A dermoscopic close-up of a skin lesion.
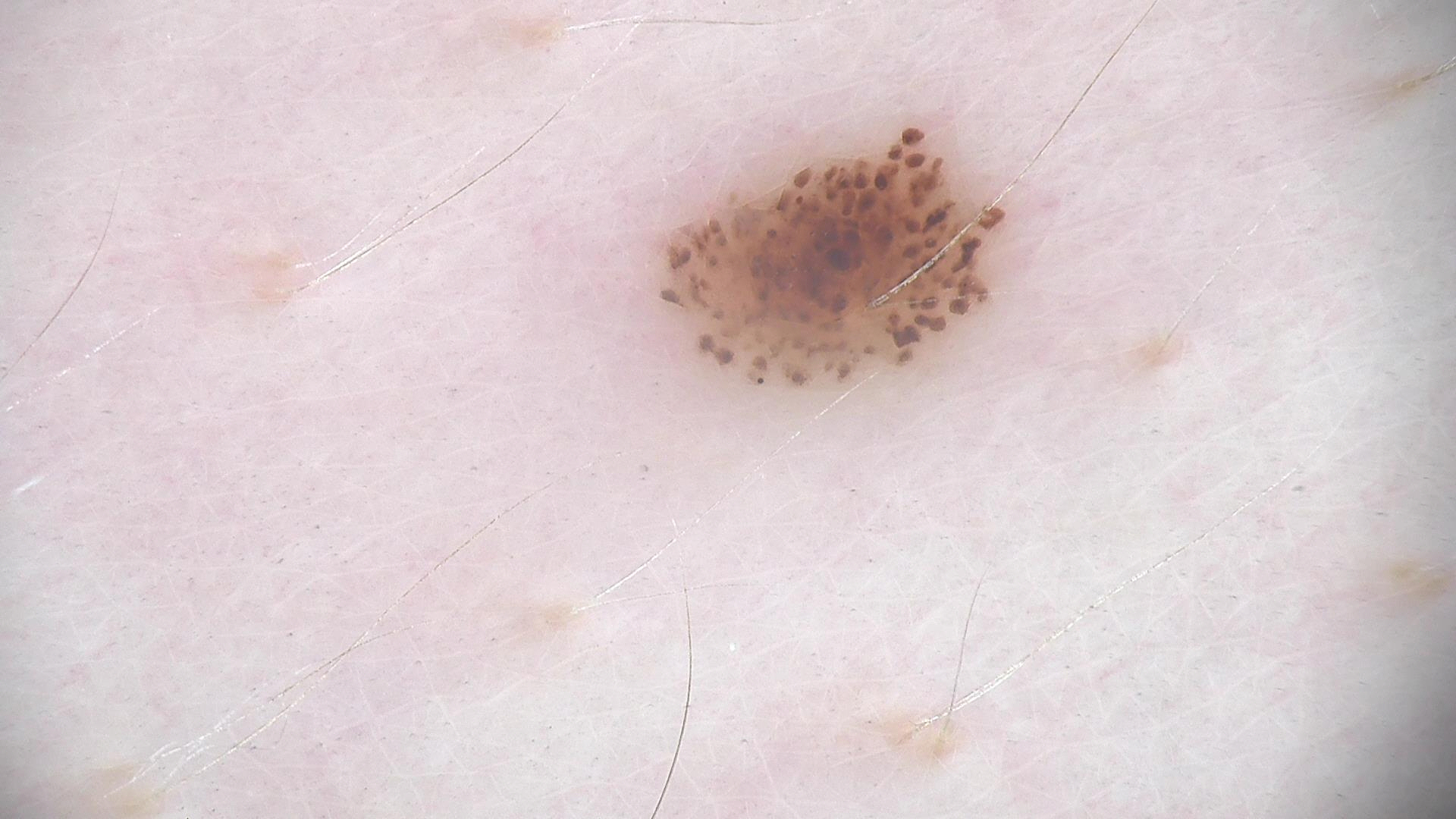Diagnosed as a dysplastic junctional nevus.